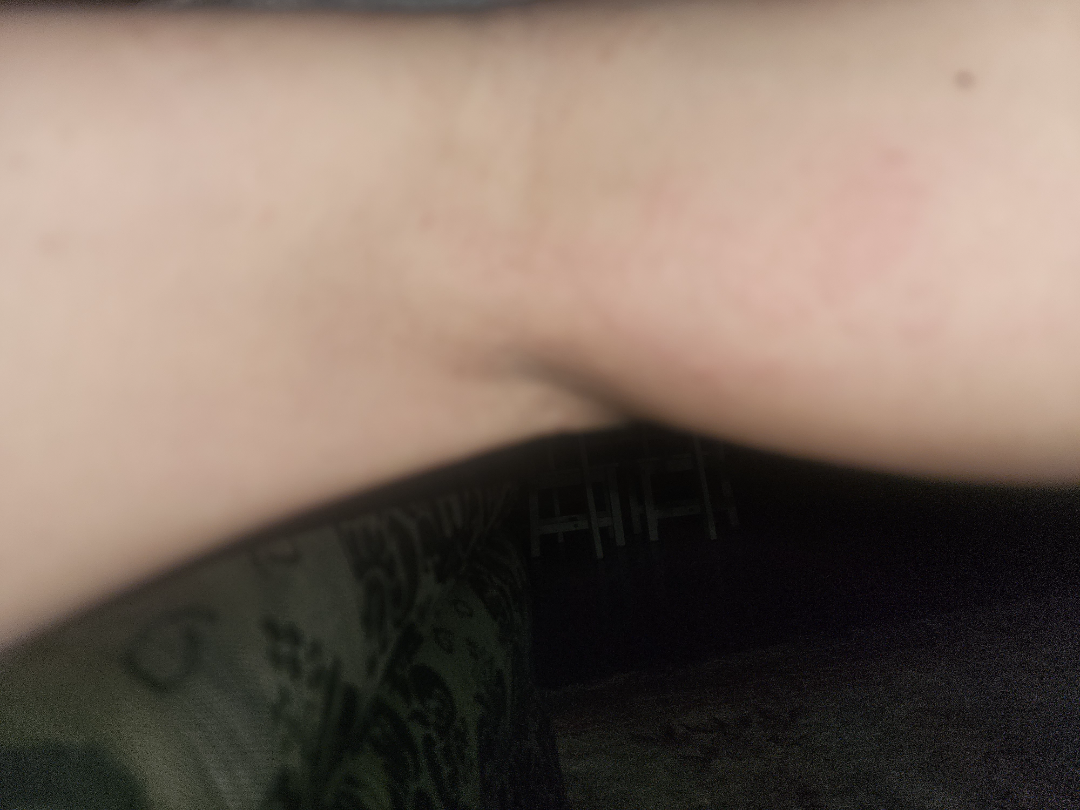Impression:
The reviewing dermatologist was unable to assign a differential diagnosis from the image.
History:
Female contributor, age 40–49. The patient considered this a rash. The patient indicates the lesion is raised or bumpy. Skin tone: Fitzpatrick phototype III; human graders estimated Monk skin tone scale 2 or 3 (two reviewer pools). The lesion involves the leg. This image was taken at a distance.